A male subject in their mid-70s · the chart notes prior malignancy (patient or family), tobacco use, pesticide exposure, and no prior skin cancer (patient or family) · a smartphone photograph of a skin lesion:
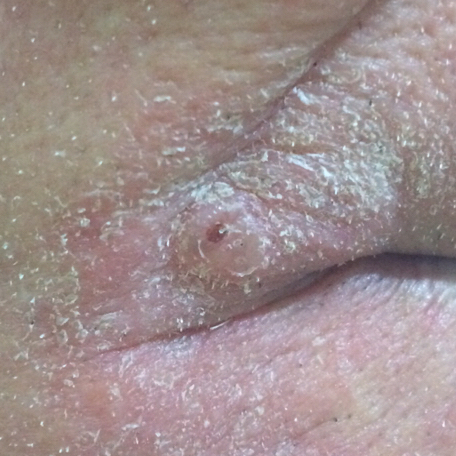| field | value |
|---|---|
| anatomic site | a lip |
| size | 6x5 mm |
| patient-reported symptoms | elevation, itching |
| diagnostic label | basal cell carcinoma (biopsy-proven) |